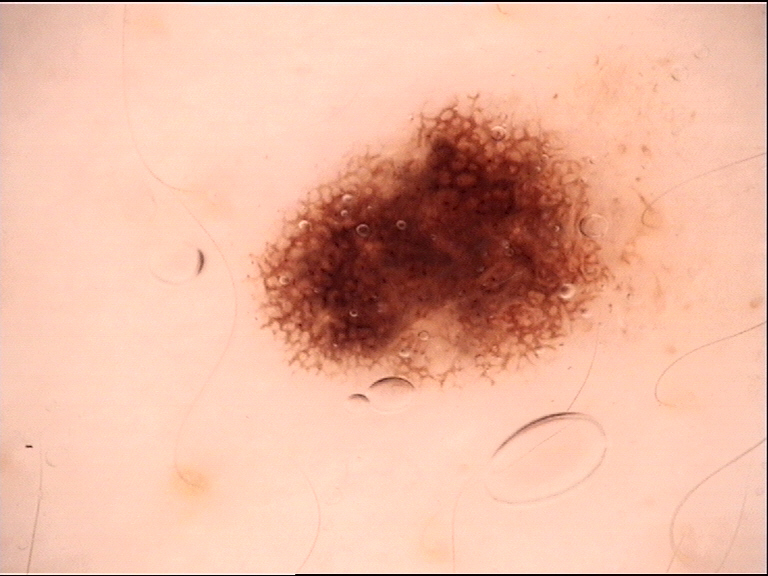diagnosis: junctional nevus (expert consensus).